A dermoscopic image of a skin lesion: 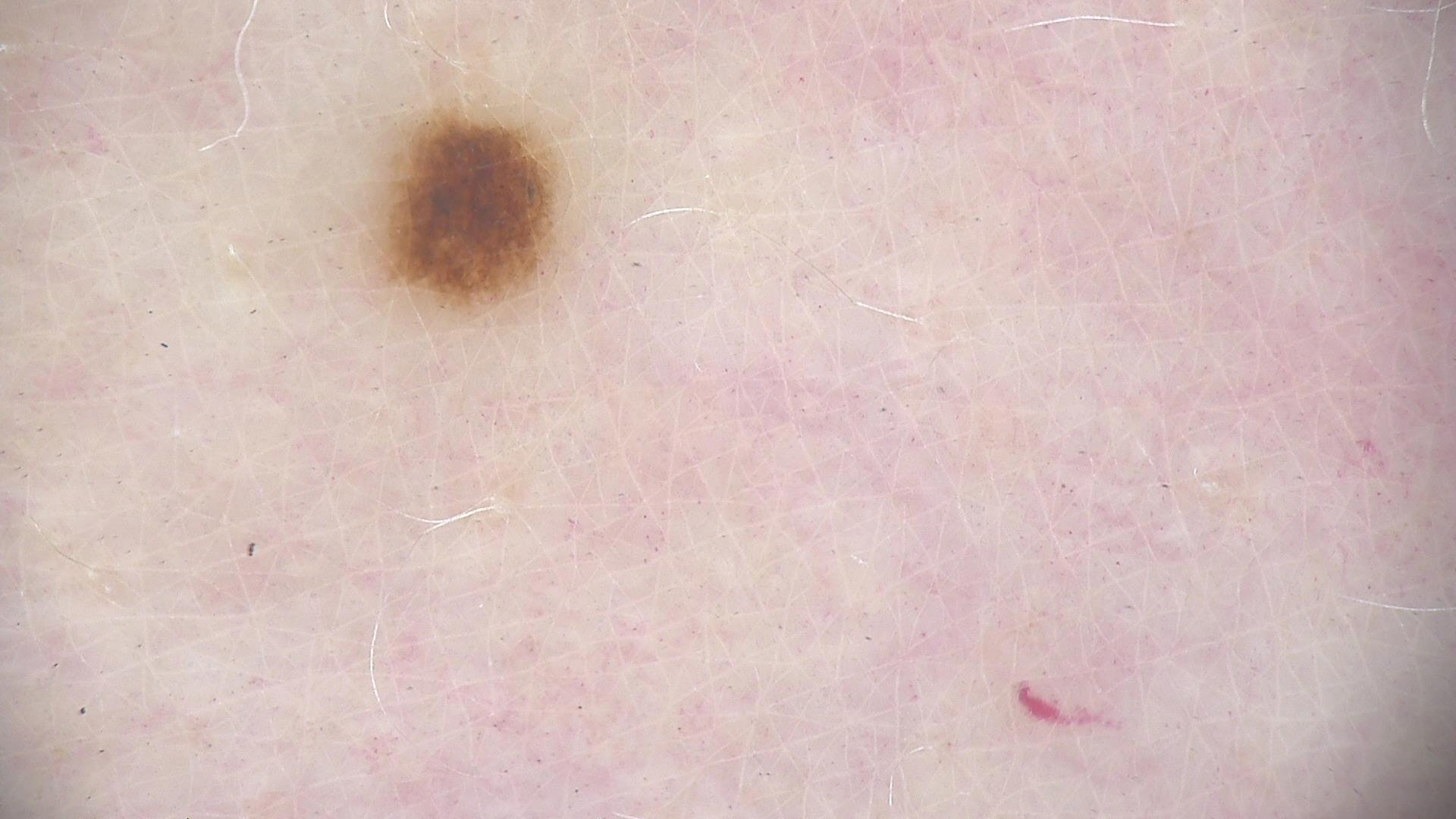Consistent with a dysplastic junctional nevus.